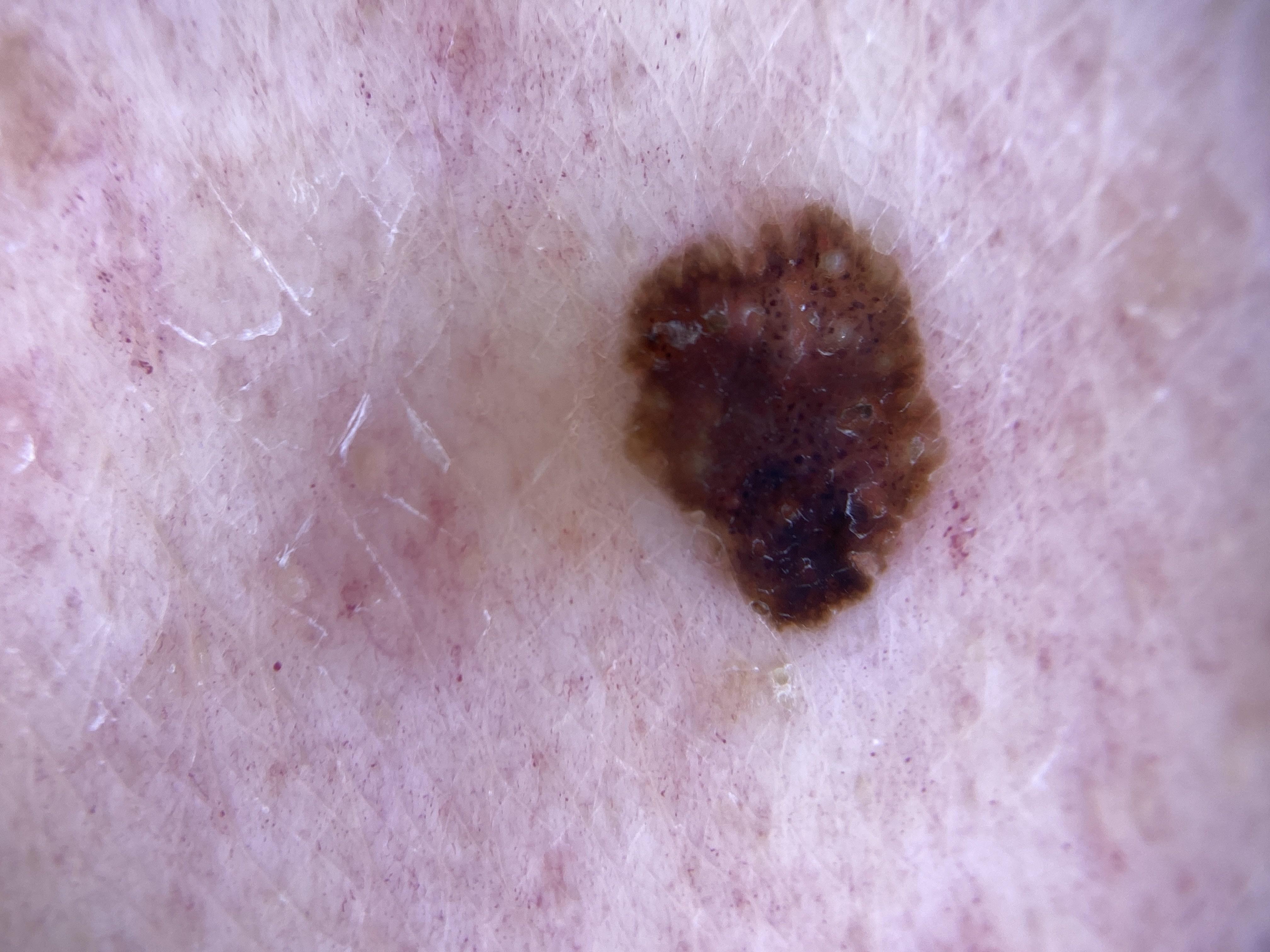Biopsy-confirmed as a seborrheic keratosis.